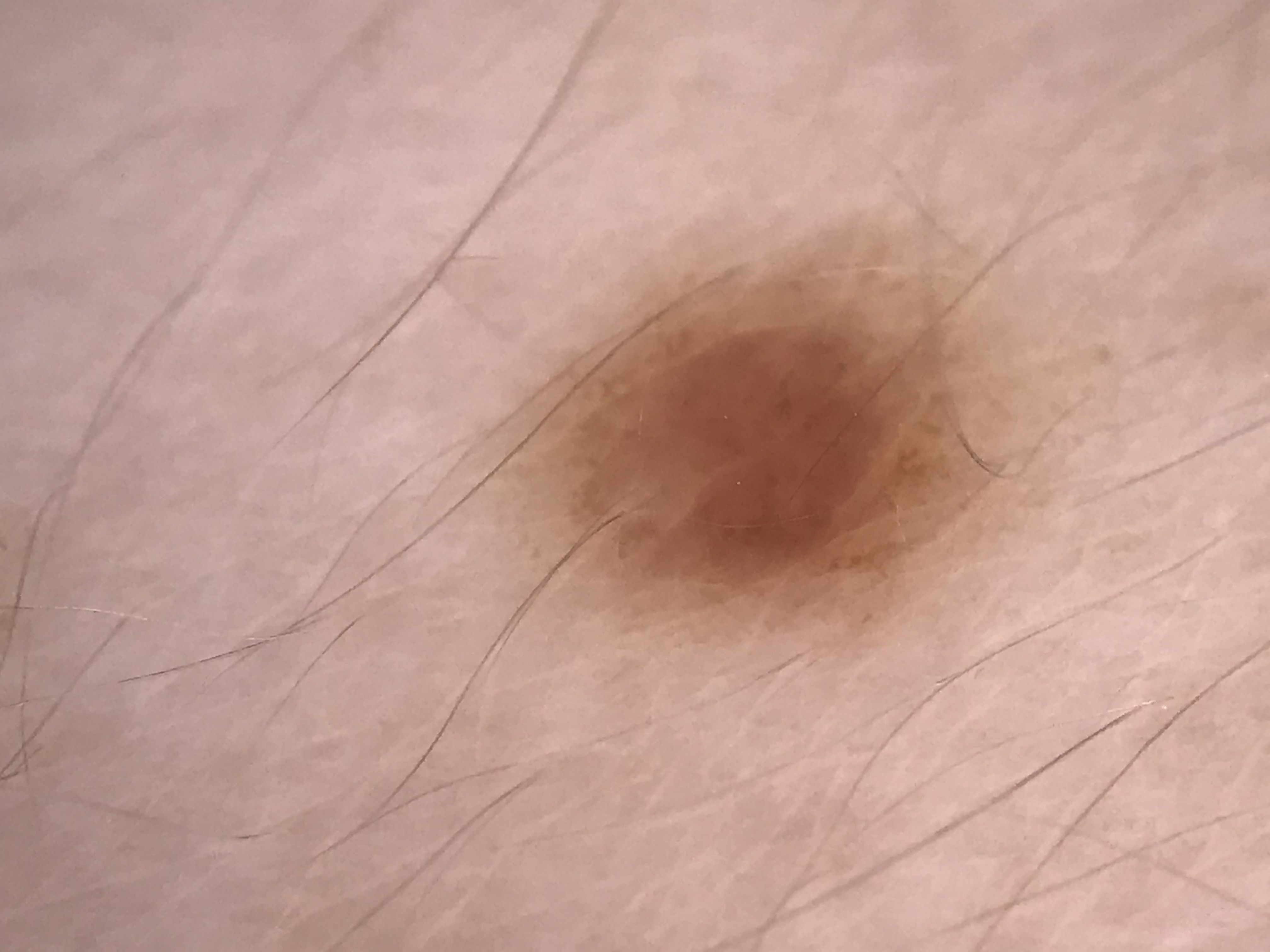A dermoscopy image of a single skin lesion.
This is a banal lesion.
Consistent with a compound nevus.